This is a close-up image: 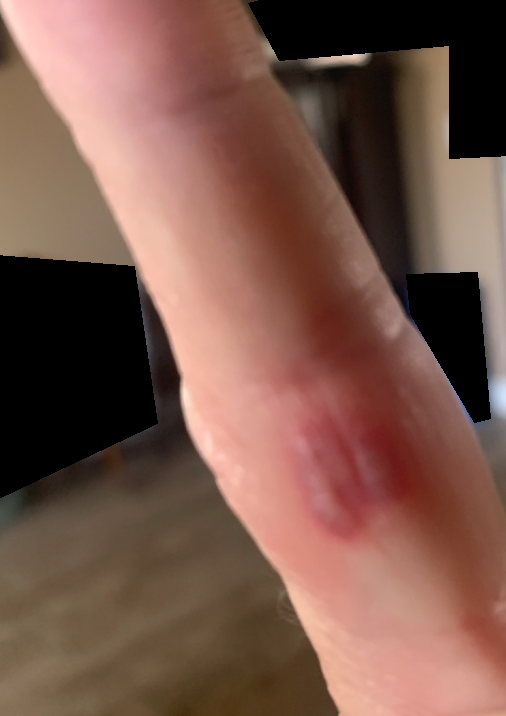The patient described the issue as a rash. Texture is reported as raised or bumpy and fluid-filled. The condition has been present for less than one week. On photographic review, the leading consideration is Herpes Simplex; also consider Insect Bite; the differential also includes Eczema.